The photograph was taken at a distance — 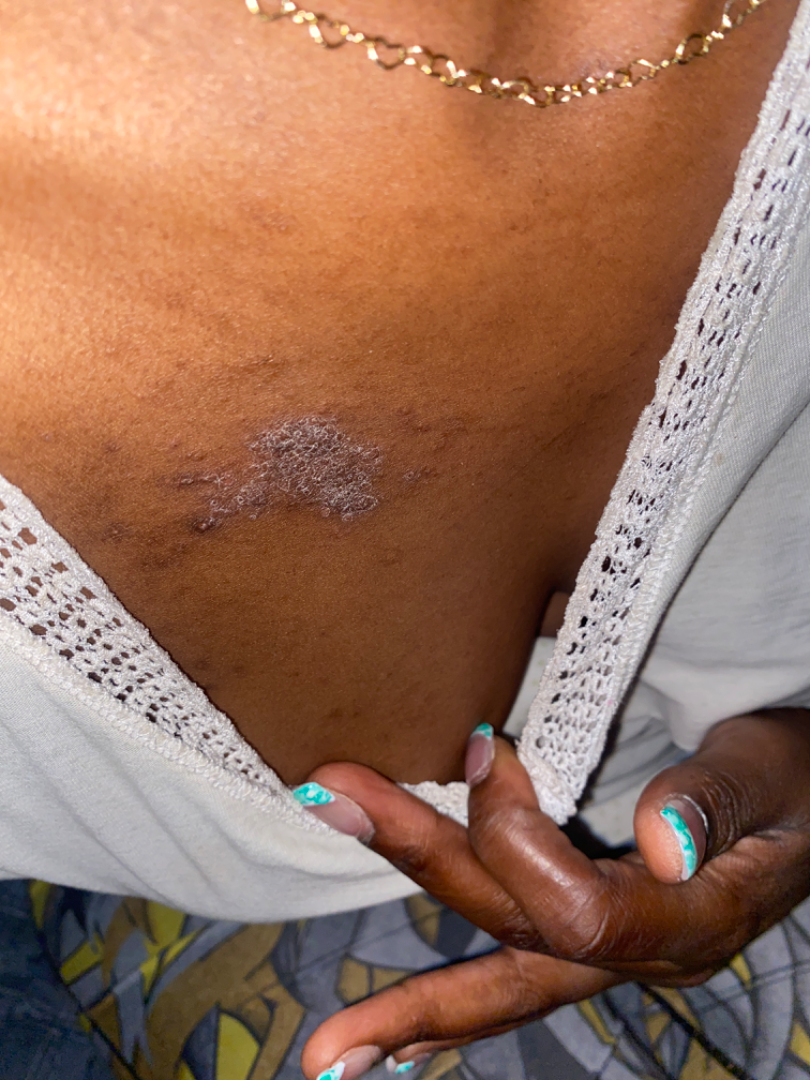Clinical context: The contributor notes bothersome appearance, darkening and itching. Skin tone: Fitzpatrick V. The condition has been present for three to twelve months. The lesion is described as raised or bumpy. Self-categorized by the patient as a rash. The patient reported no systemic symptoms. Assessment: The differential, in no particular order, includes Lichen planus/lichenoid eruption and Chronic dermatitis, NOS.